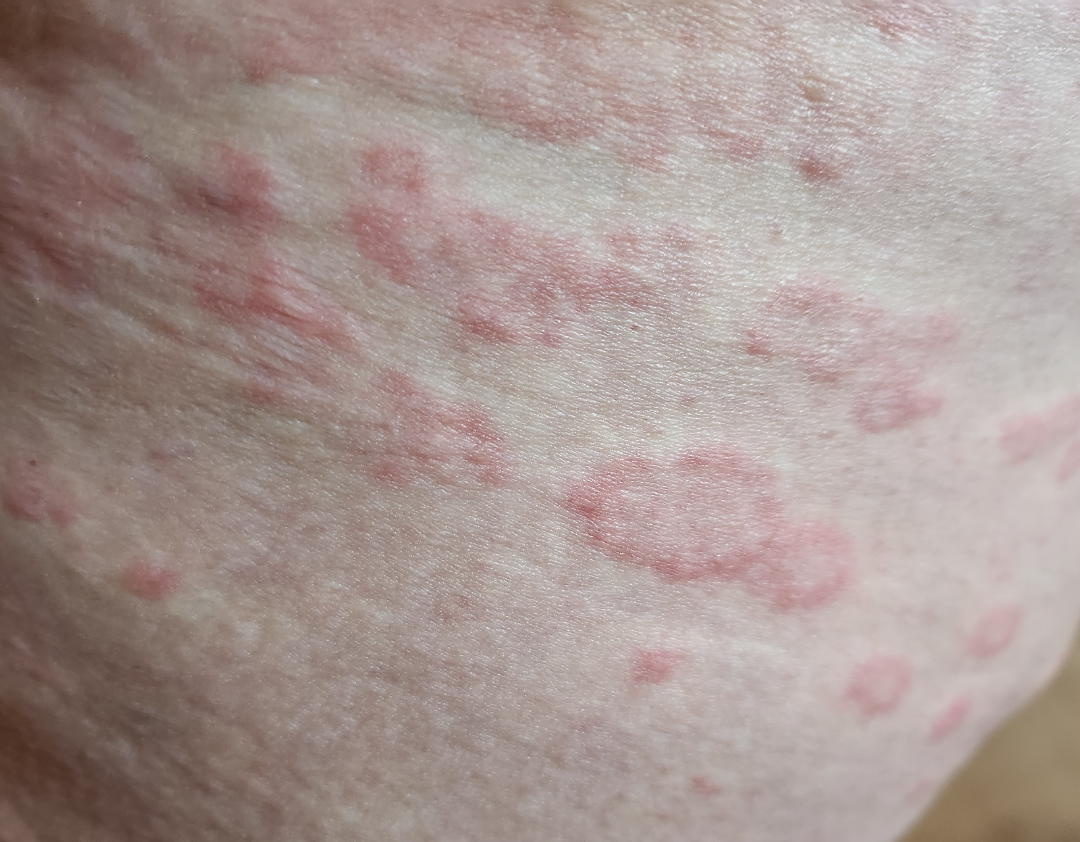Impression:
Single-reviewer assessment: most likely Granuloma annulare; an alternative is Annular erythema.